A female patient aged approximately 35. The chart documents no melanoma in first-degree relatives and no previous melanoma — 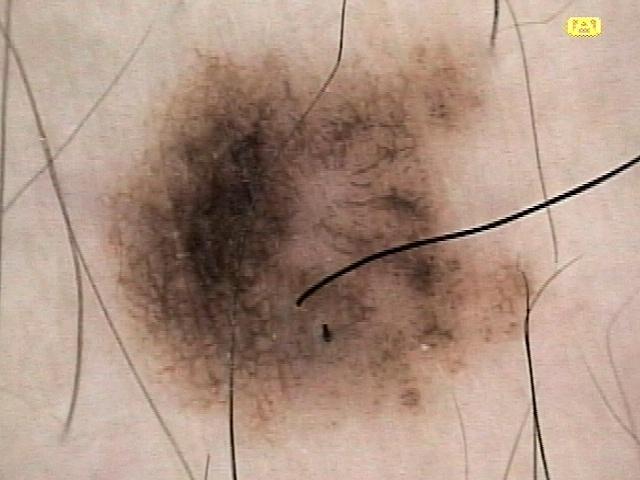Q: What is the diagnosis?
A: Nevus (biopsy-proven)